A dermoscopic close-up of a skin lesion.
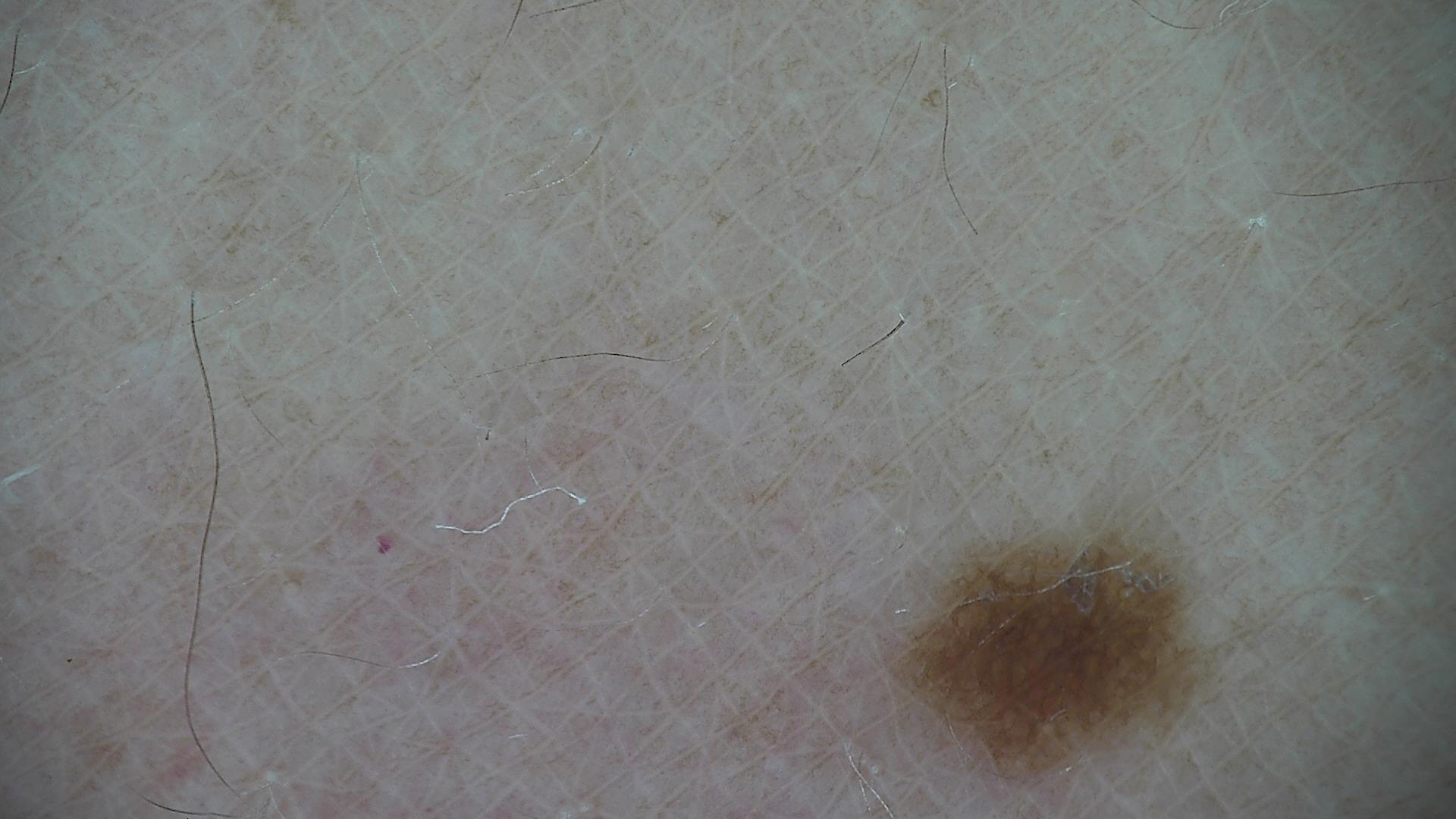Consistent with a benign lesion — a dysplastic junctional nevus.